A dermatoscopic image of a skin lesion.
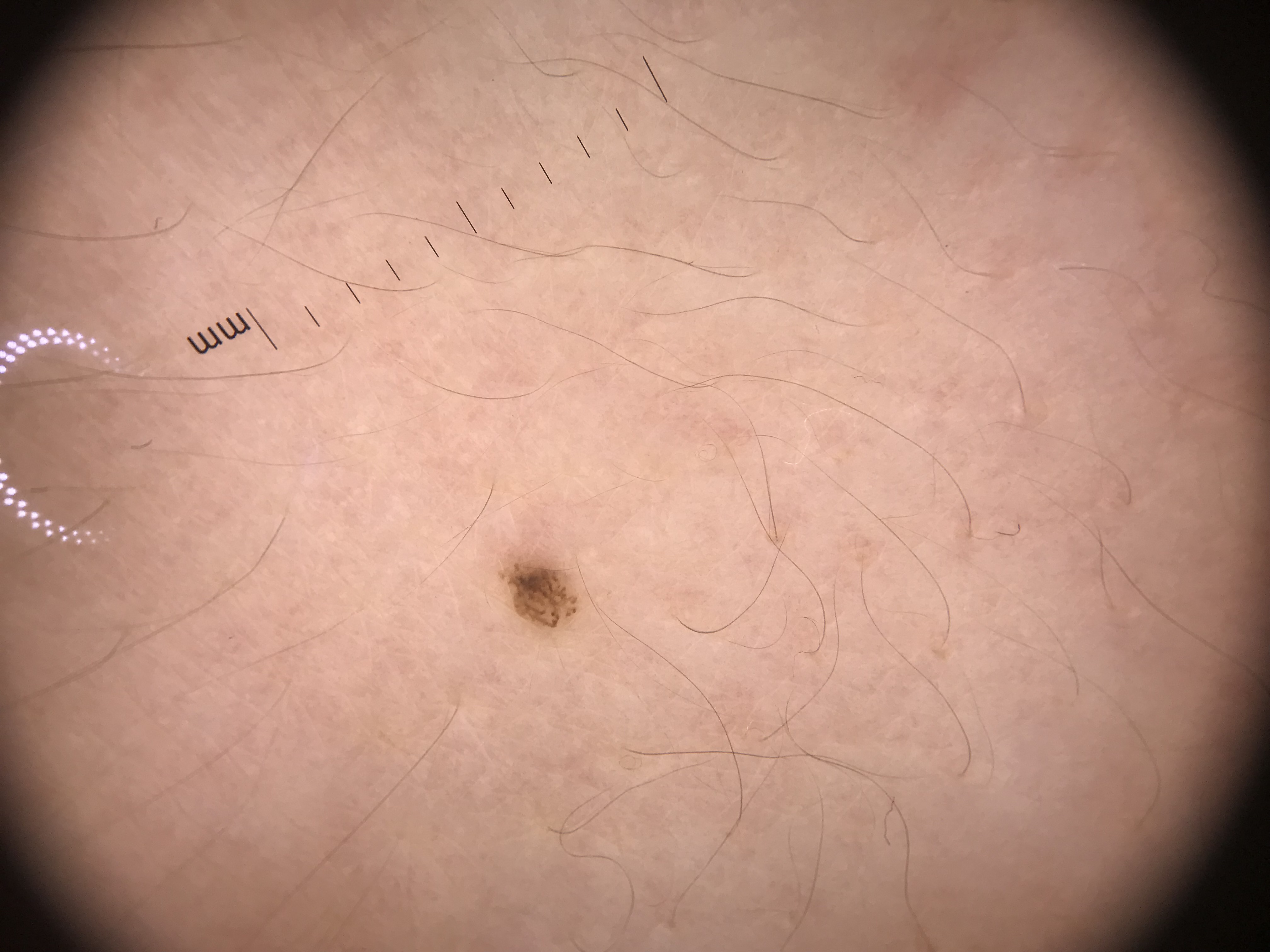Diagnosed as a banal lesion — a junctional nevus.